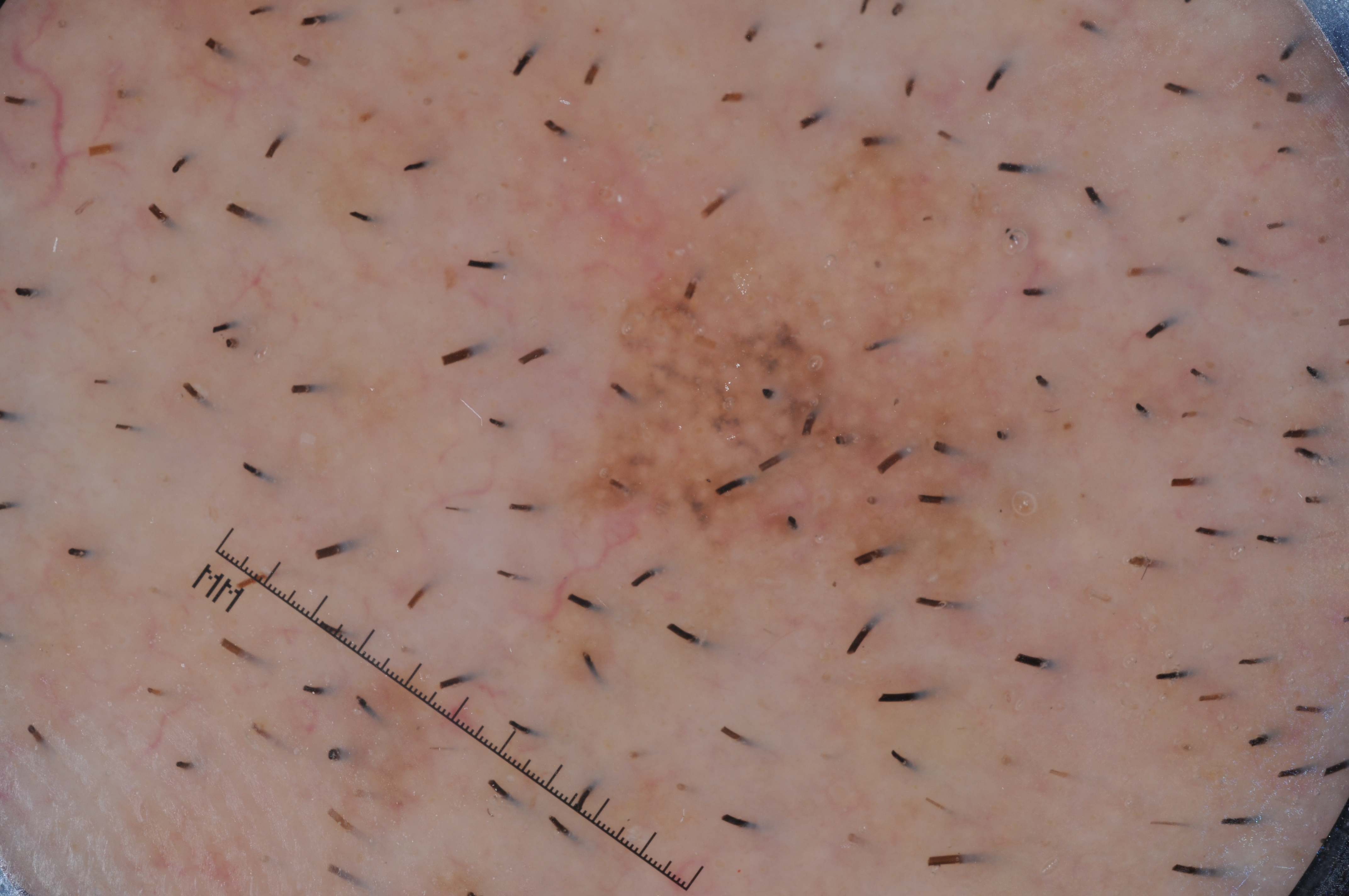patient: male, in their 70s
imaging: dermoscopy
lesion size: ~10% of the field
bounding box: x1=559, y1=231, x2=1054, y2=588
dermoscopic findings: milia-like cysts
assessment: a melanoma, a malignancy